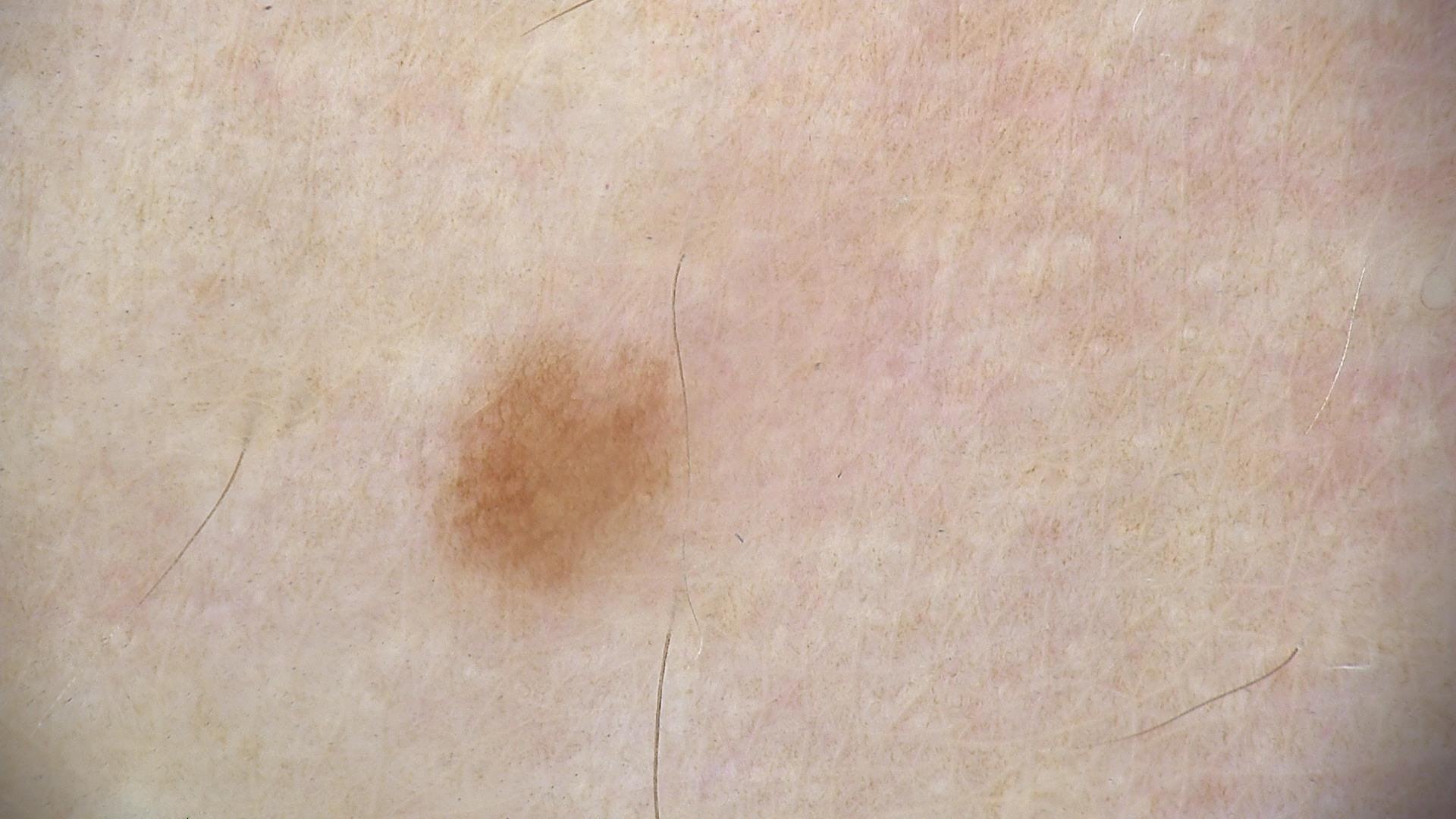A skin lesion imaged with a dermatoscope.
Classified as a dysplastic junctional nevus.